A dermoscopic image of a skin lesion.
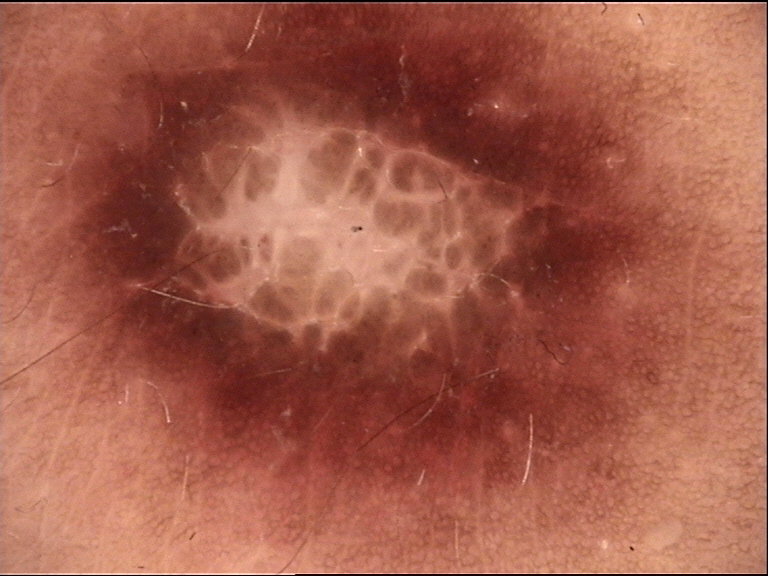Diagnosed as a benign lesion — a dermatofibroma.